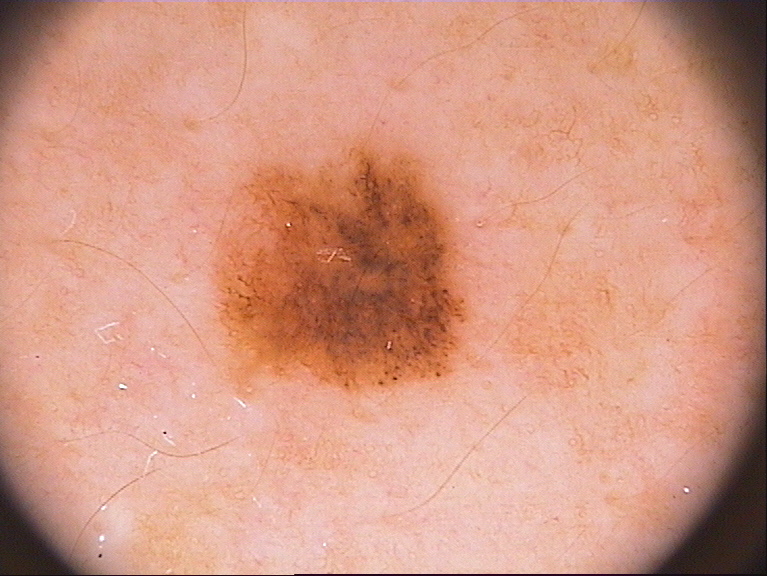Case summary:
A dermoscopic image of a skin lesion. As (left, top, right, bottom), the lesion is bounded by <bbox>211, 127, 473, 392</bbox>.
Impression:
The clinical diagnosis was a melanocytic nevus, a benign skin lesion.